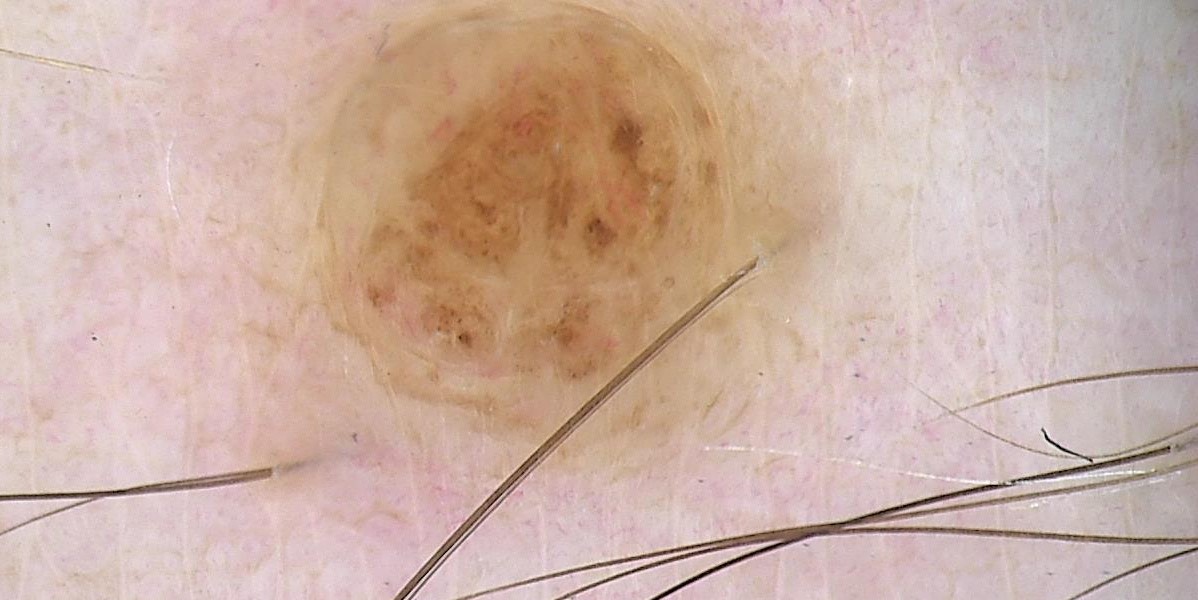image type: dermoscopy, class: dermal nevus (expert consensus).